A dermoscopic image of a skin lesion:
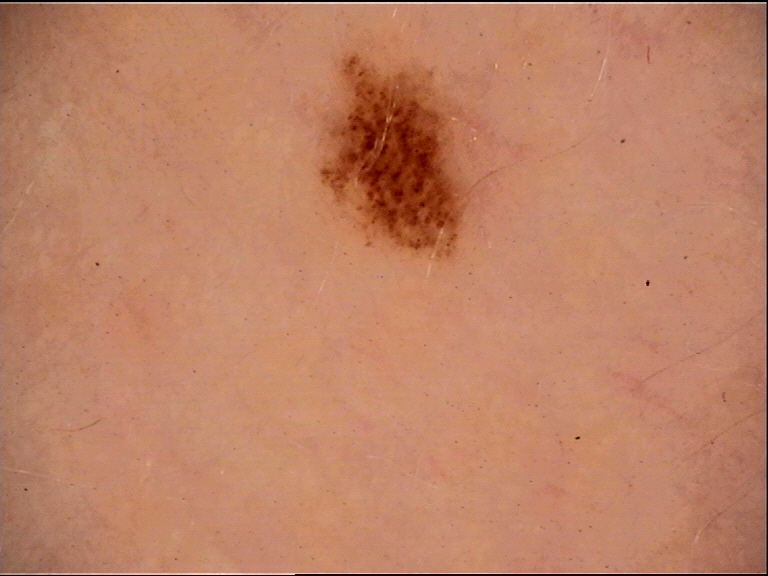Diagnosed as a dysplastic junctional nevus.